Symptoms reported: itching and bothersome appearance · reported duration is one to four weeks · the lesion involves the leg · the patient considered this skin that appeared healthy to them · a close-up photograph · the patient reported no systemic symptoms · the patient is 30–39, female · texture is reported as rough or flaky:
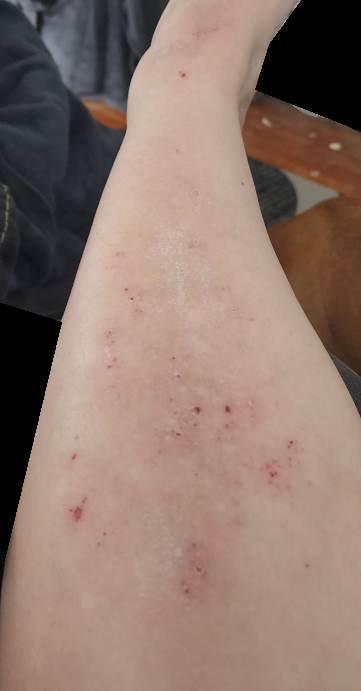Q: What is the dermatologist's impression?
A: one reviewing dermatologist: the leading impression is Eczema; also on the differential is Stasis Dermatitis; with consideration of Allergic Contact Dermatitis